Female subject, age 18–29; the affected area is the leg; a close-up photograph:
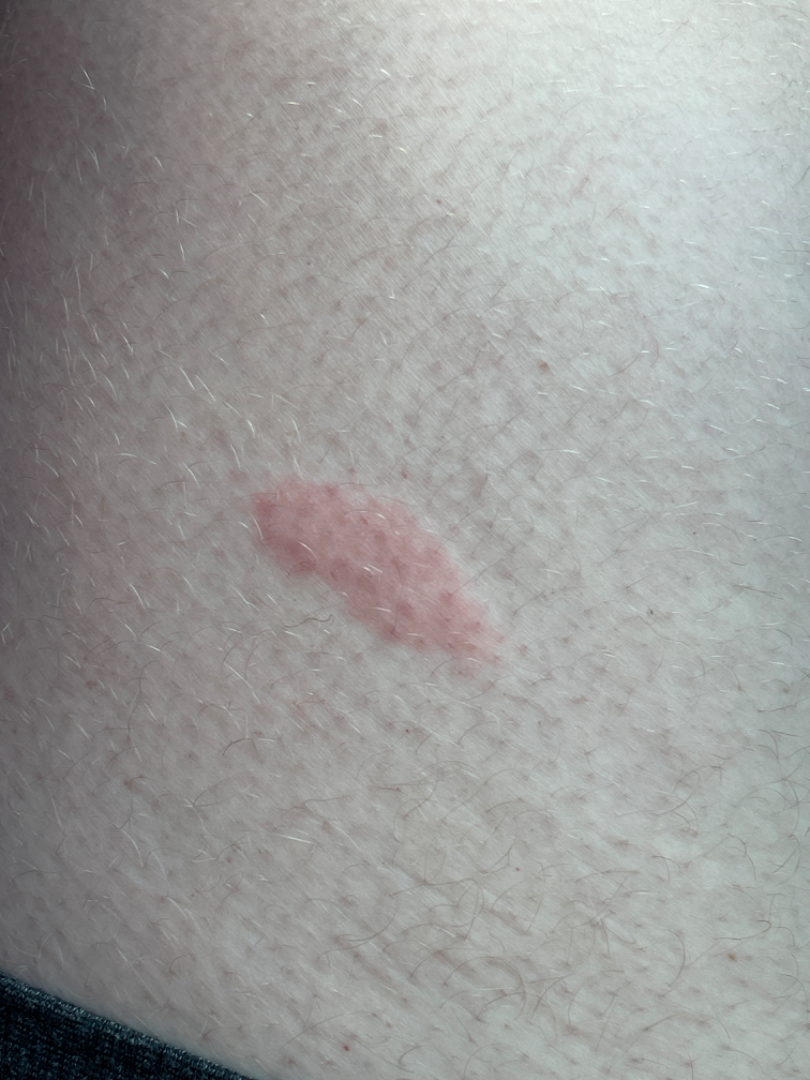assessment: indeterminate from the photograph.